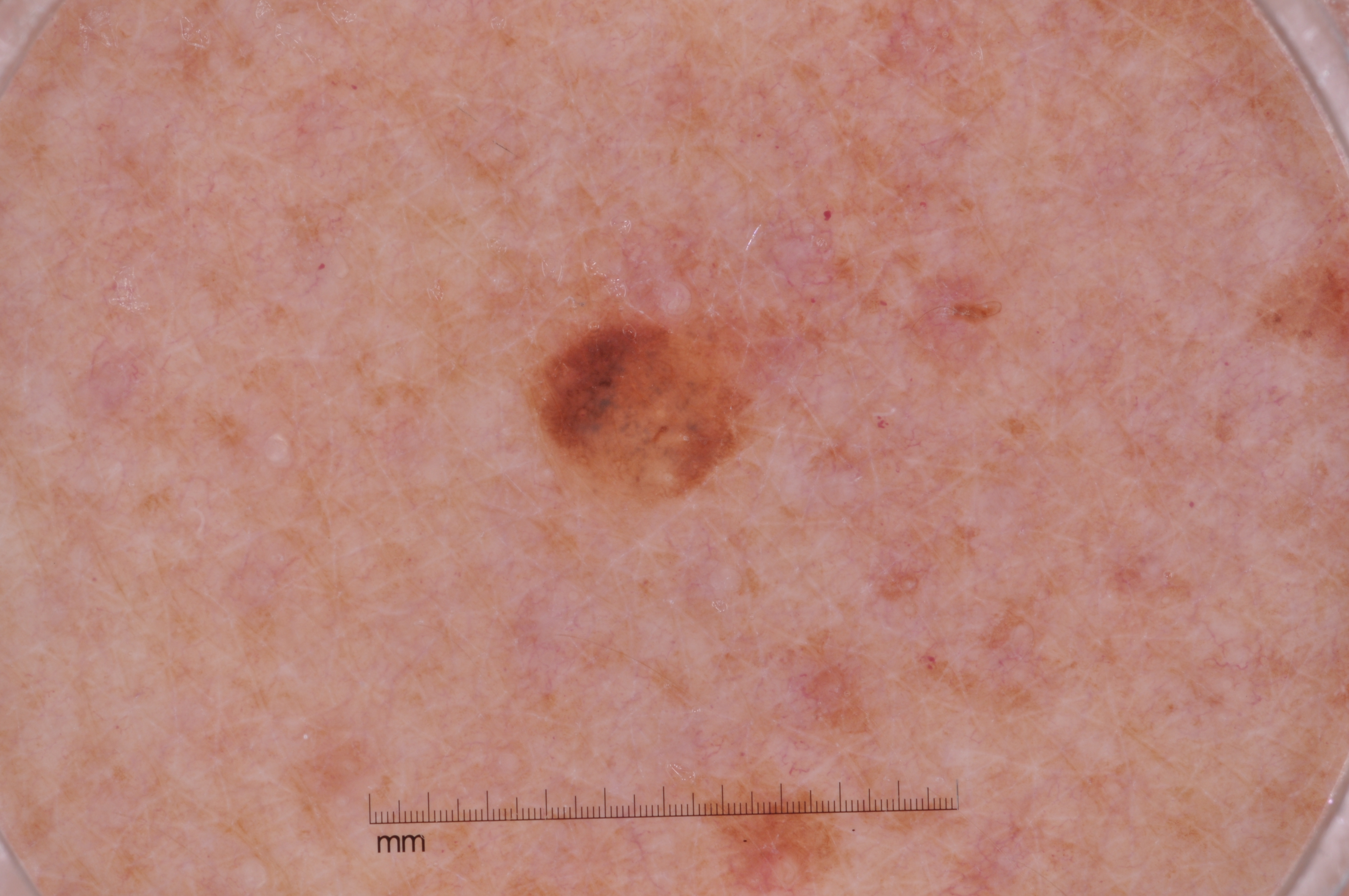A dermoscopic view of a skin lesion.
The subject is a female about 50 years old.
The lesion covers approximately 3% of the dermoscopic field.
With coordinates (x1, y1, x2, y2), the lesion is located at 517/243/794/509.
Dermoscopically, the lesion shows pigment network, with no negative network, milia-like cysts, or streaks.
Consistent with a melanocytic nevus, a benign skin lesion.